Close-up view; the patient is male; the lesion involves the top or side of the foot, head or neck, arm, back of the hand and leg — 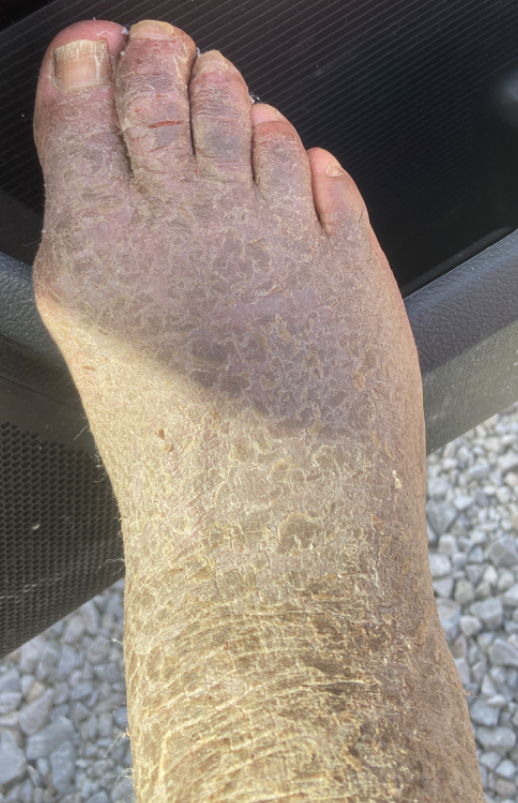Q: What is the differential diagnosis?
A: Ichthyosis (most likely)